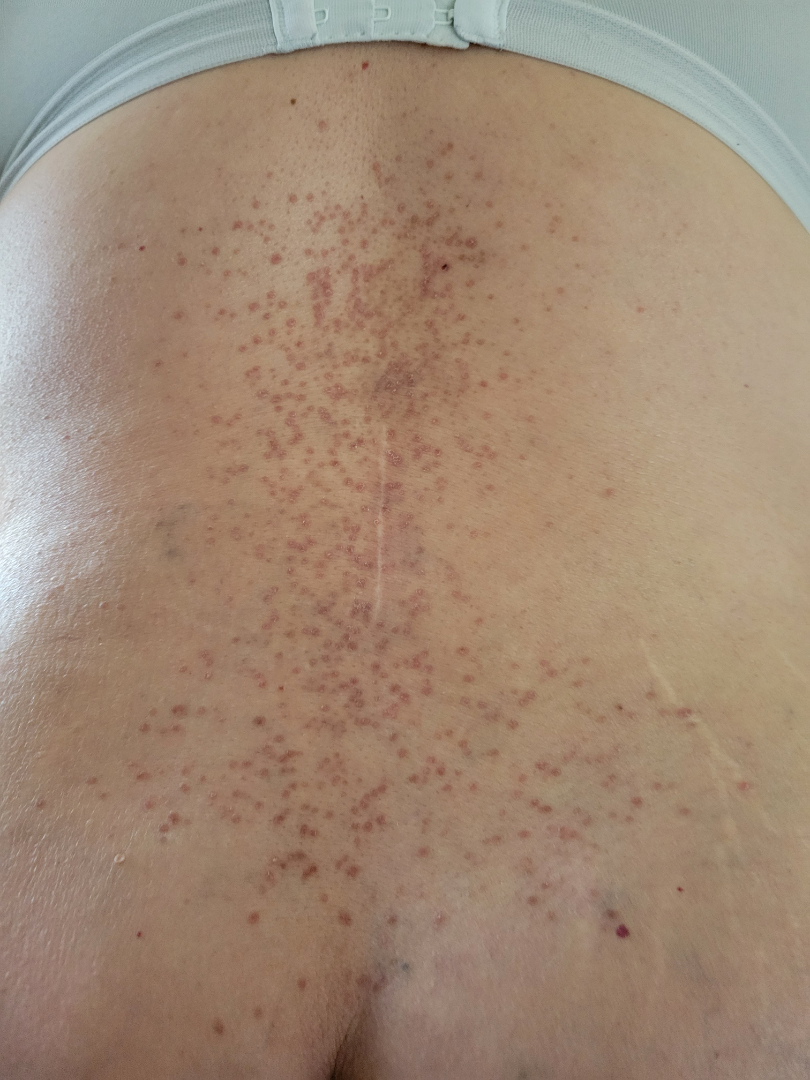clinical impression = most consistent with Psoriasis.